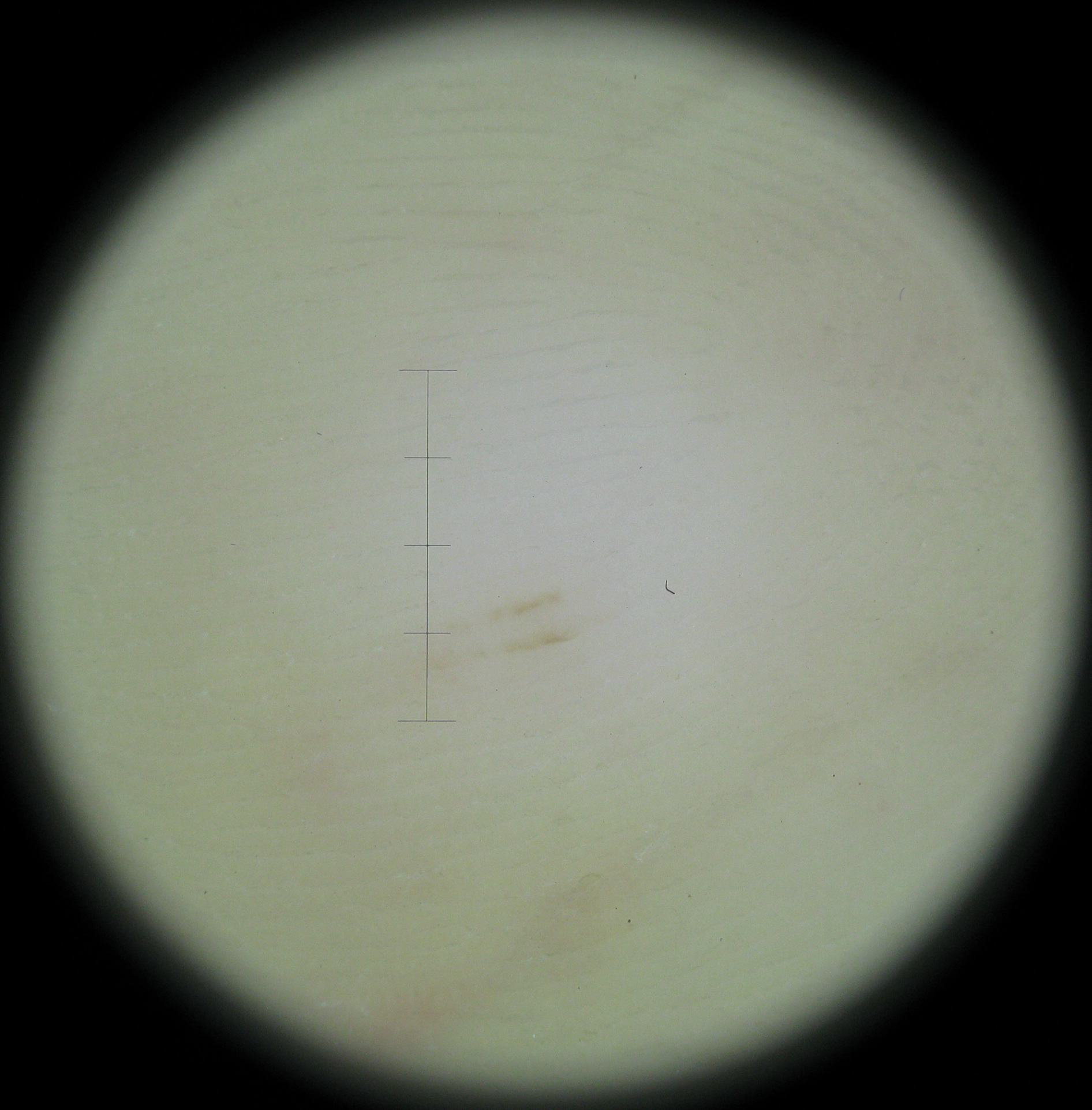subtype: banal; class: acral junctional nevus (expert consensus).